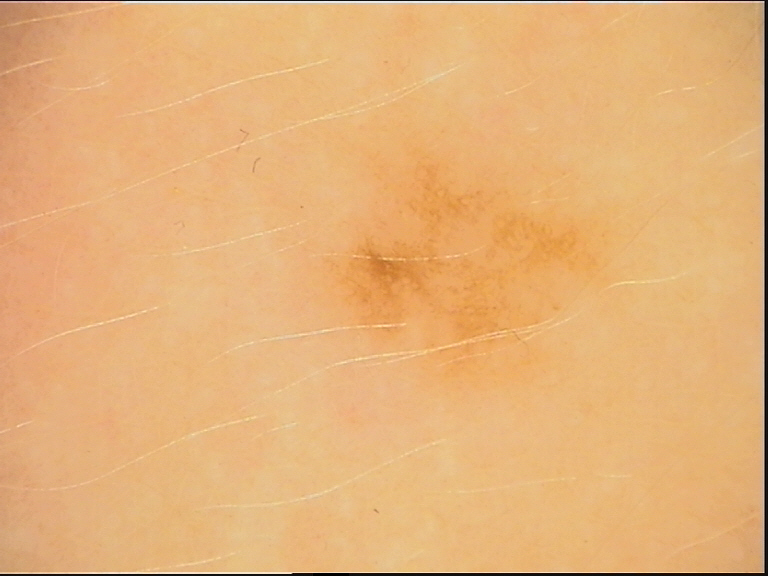Impression: The diagnosis was a dysplastic junctional nevus.